Dermoscopy of a skin lesion.
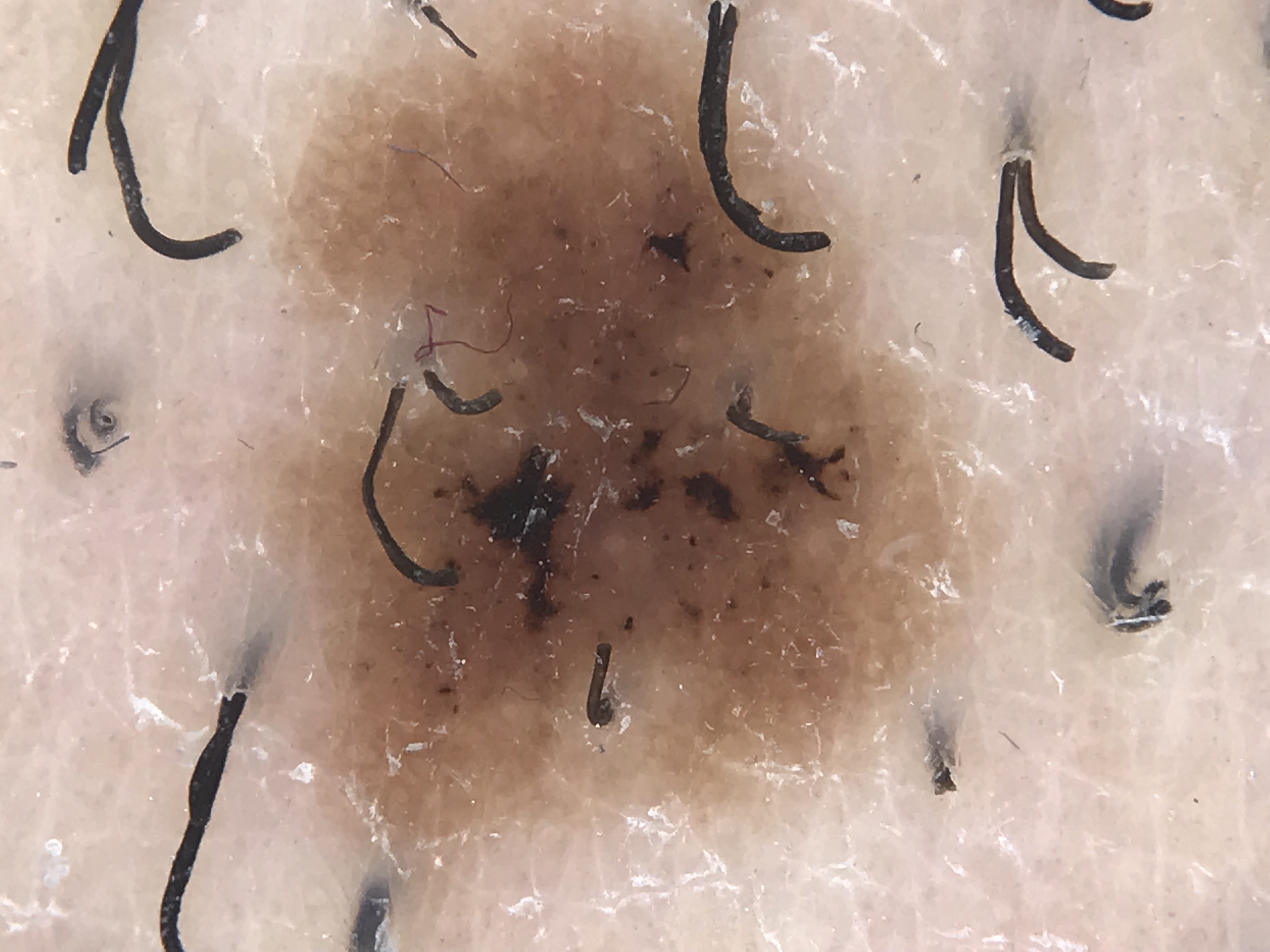Conclusion: Consistent with a compound nevus.